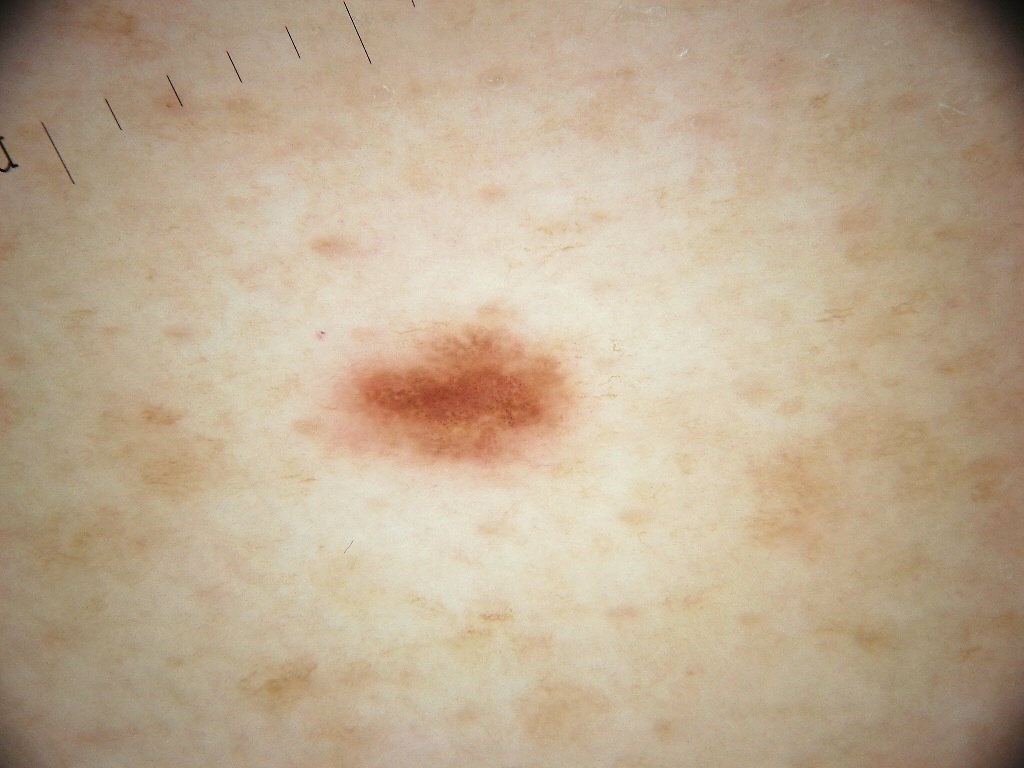subject = female, in their mid- to late 40s
imaging = dermatoscopic image of a skin lesion
lesion location = 301 293 592 483
lesion extent = ~5% of the field
dermoscopic pattern = globules and negative network; absent: streaks, pigment network, and milia-like cysts
diagnostic label = a melanocytic nevus, a benign skin lesion